Male patient, age 18–29. This image was taken at a distance. The arm is involved: 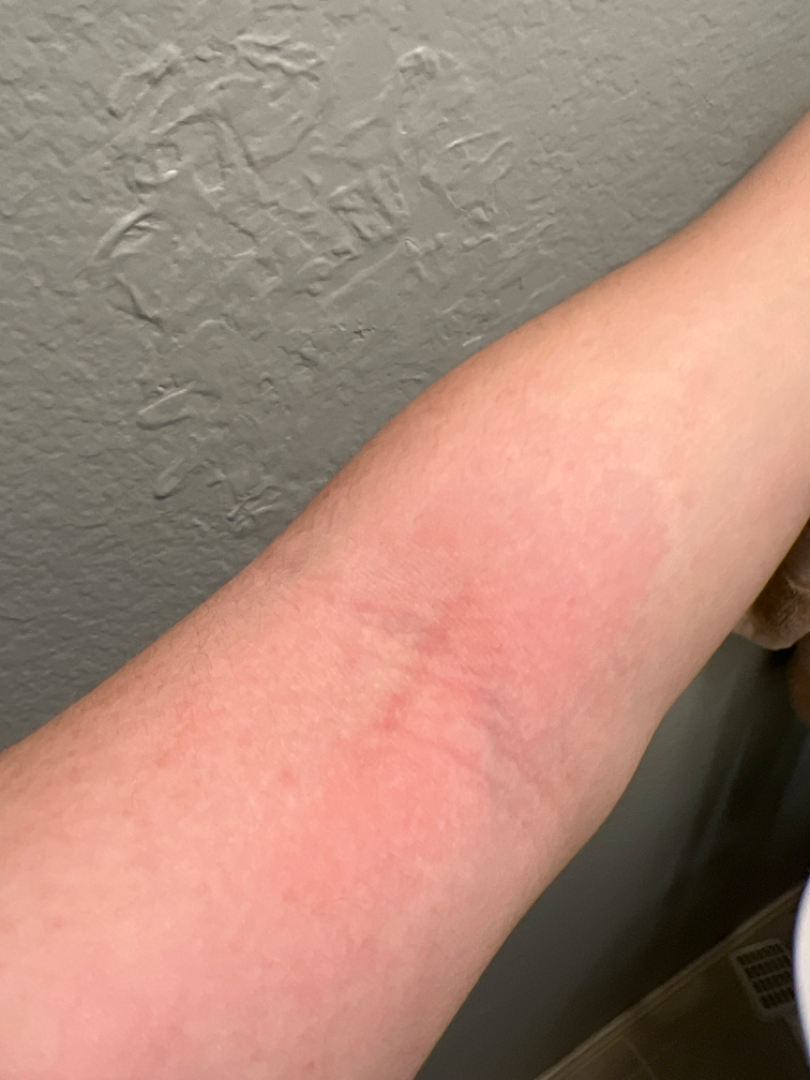Assessment: On dermatologist assessment of the image: the leading consideration is Eczema; also consider Urticaria; also raised was Irritant Contact Dermatitis; less likely is Acute dermatitis, NOS; lower on the differential is Allergic Contact Dermatitis; less probable is Cellulitis.